The lesion involves the back of the torso, leg, arm and back of the hand; the contributor is 50–59, male; the photograph is a close-up of the affected area: 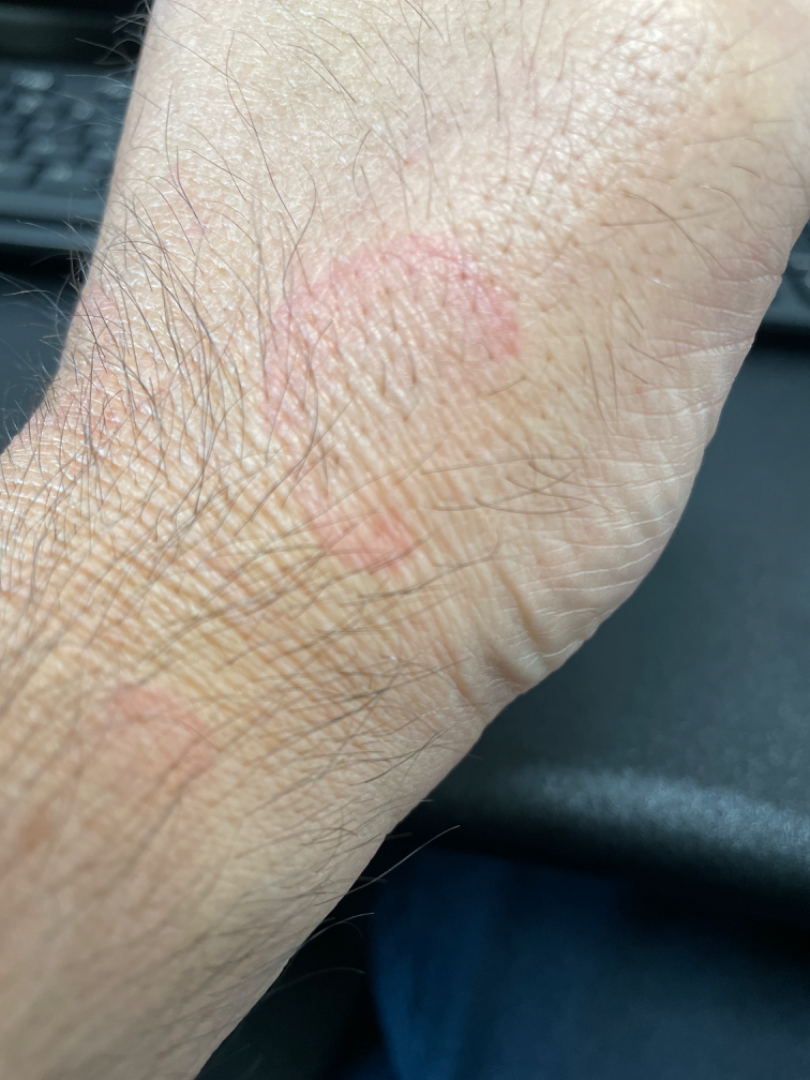{
  "assessment": "could not be assessed",
  "texture": "flat",
  "skin_tone": {
    "fitzpatrick": "III",
    "monk_skin_tone": [
      1,
      2
    ]
  },
  "systemic_symptoms": [
    "fatigue",
    "chills"
  ]
}